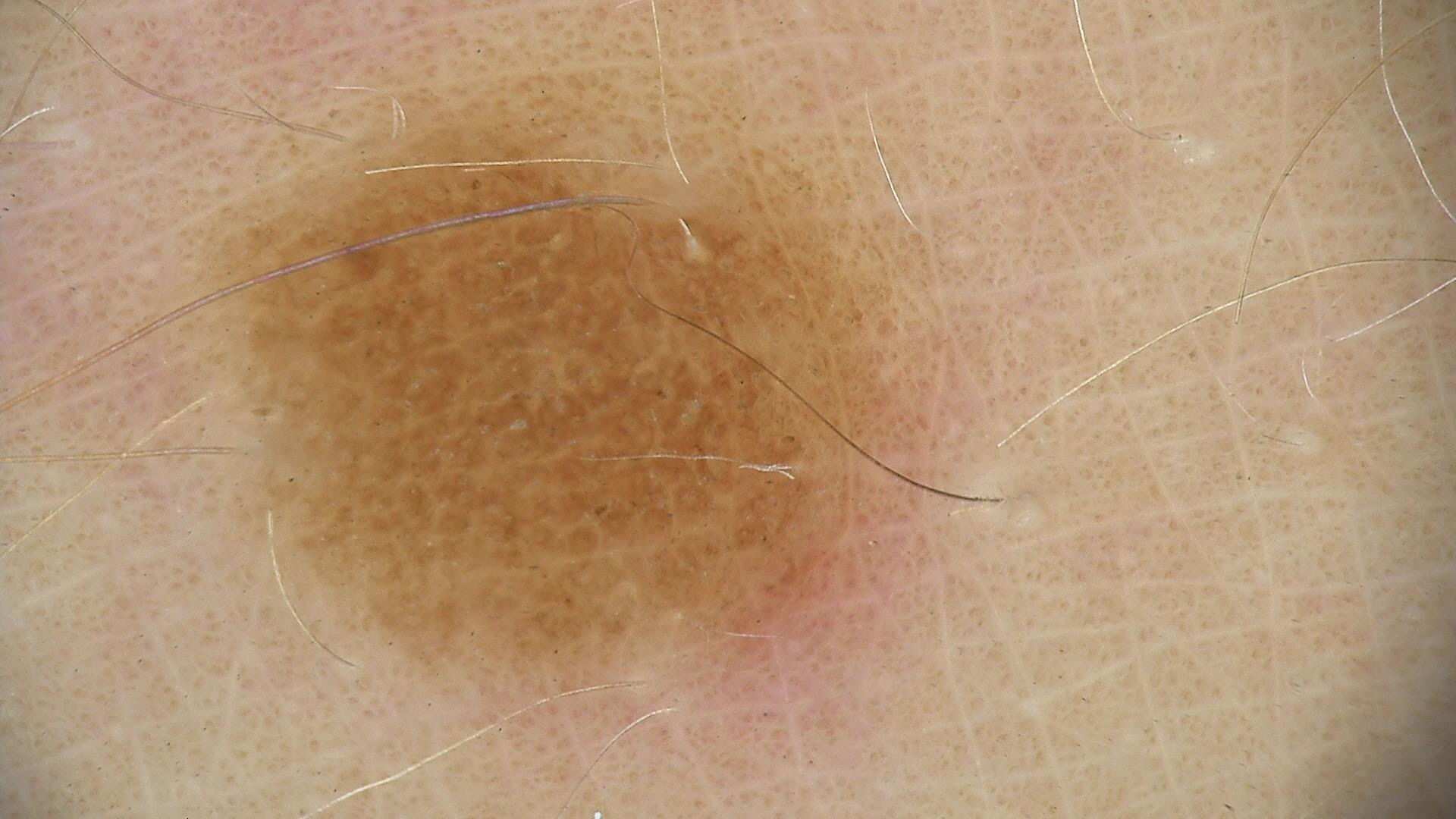A dermoscopic close-up of a skin lesion. Labeled as a dysplastic compound nevus.